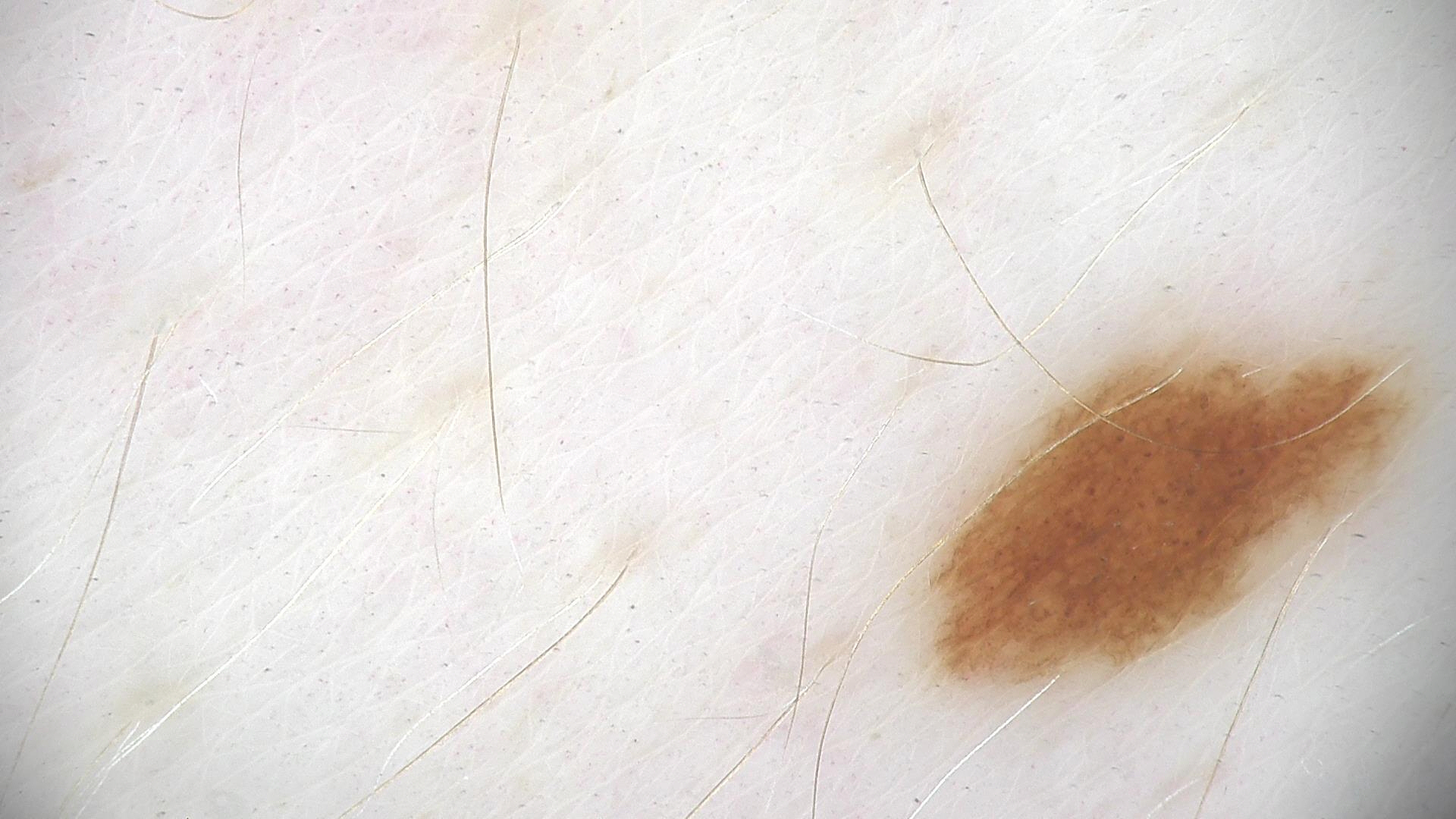A dermoscopy image of a single skin lesion.
The diagnostic label was a benign lesion — a dysplastic junctional nevus.